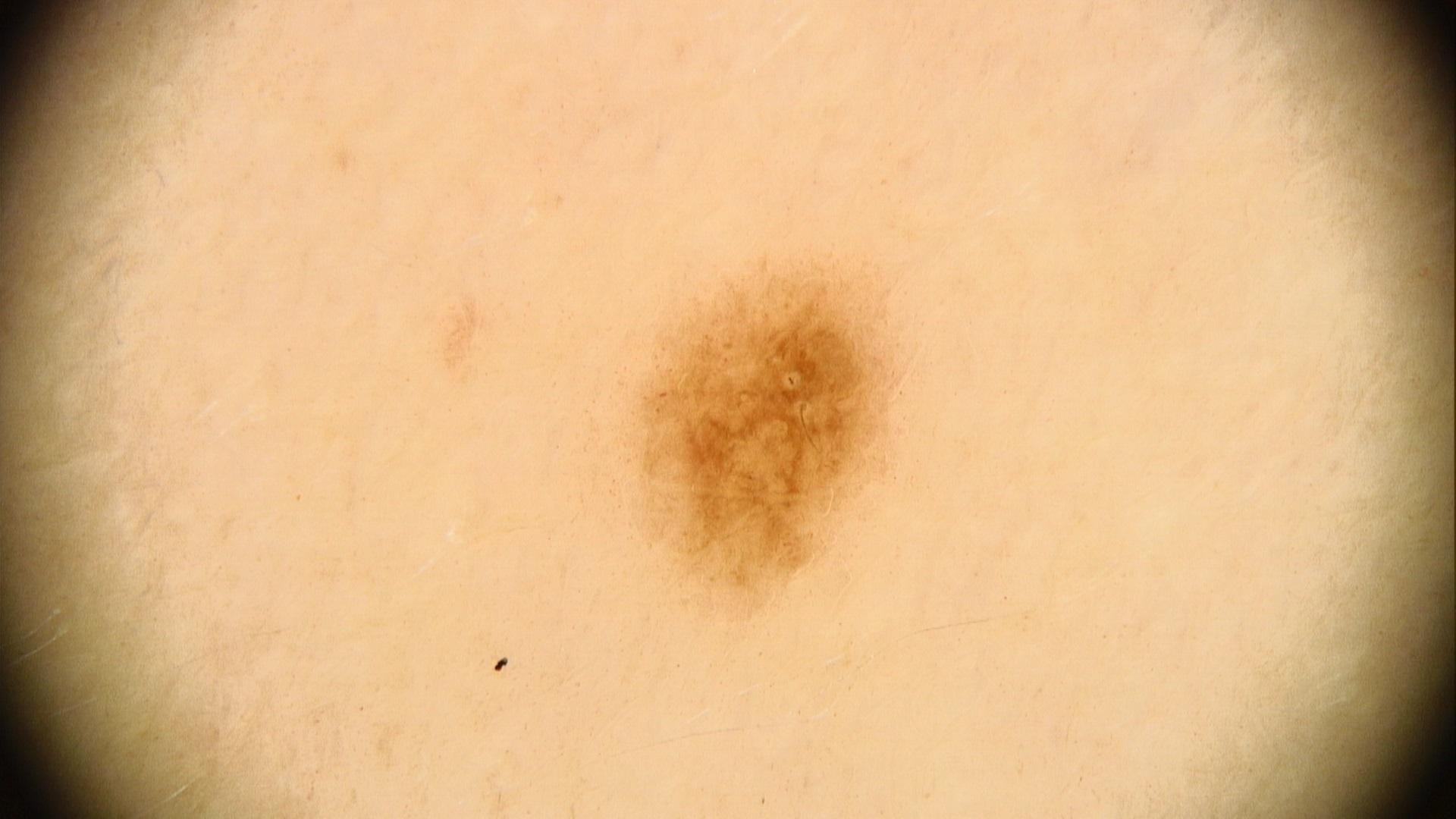A dermoscopic image of a skin lesion. The patient was assessed as Fitzpatrick phototype III. The chart records melanoma in a first-degree relative. Located on the trunk (the anterior trunk). Clinically diagnosed as a benign lesion — a nevus.